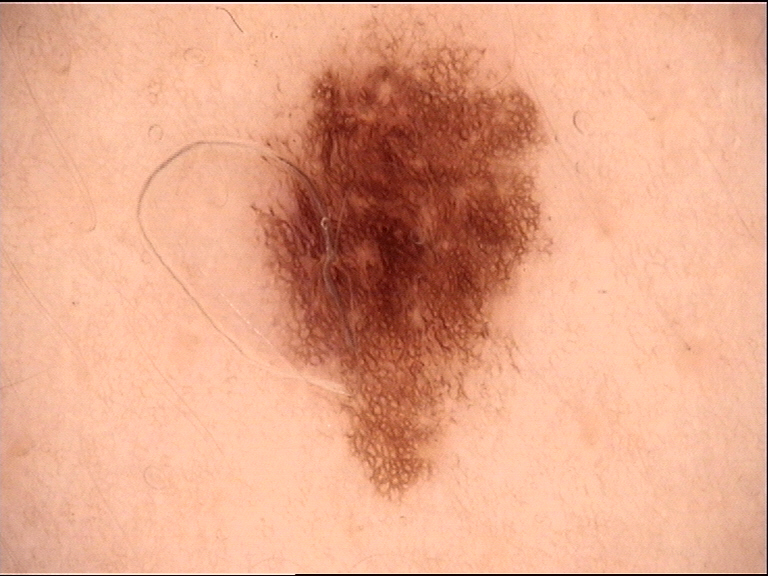The diagnostic label was a benign lesion — a dysplastic junctional nevus.